Male contributor, age 18–29. The photograph was taken at an angle. The affected area is the leg: 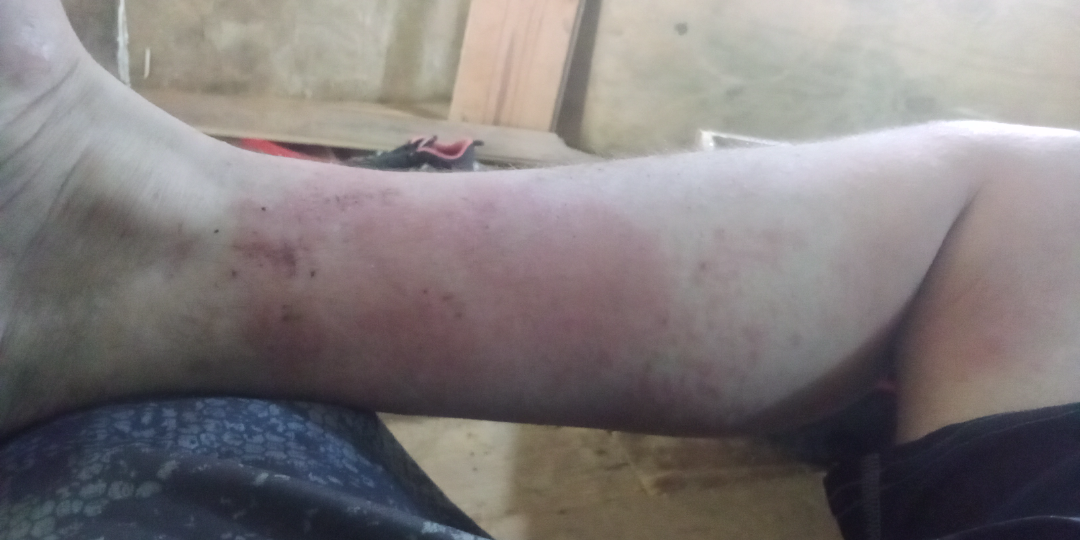  assessment: could not be assessed
  symptoms:
    - pain
    - itching
  texture:
    - flat
    - raised or bumpy
  skin_tone:
    fitzpatrick: III
    fitzpatrick_source: self_reported
  duration: less than one week
  patient_category: a rash